Dermoscopy of a skin lesion.
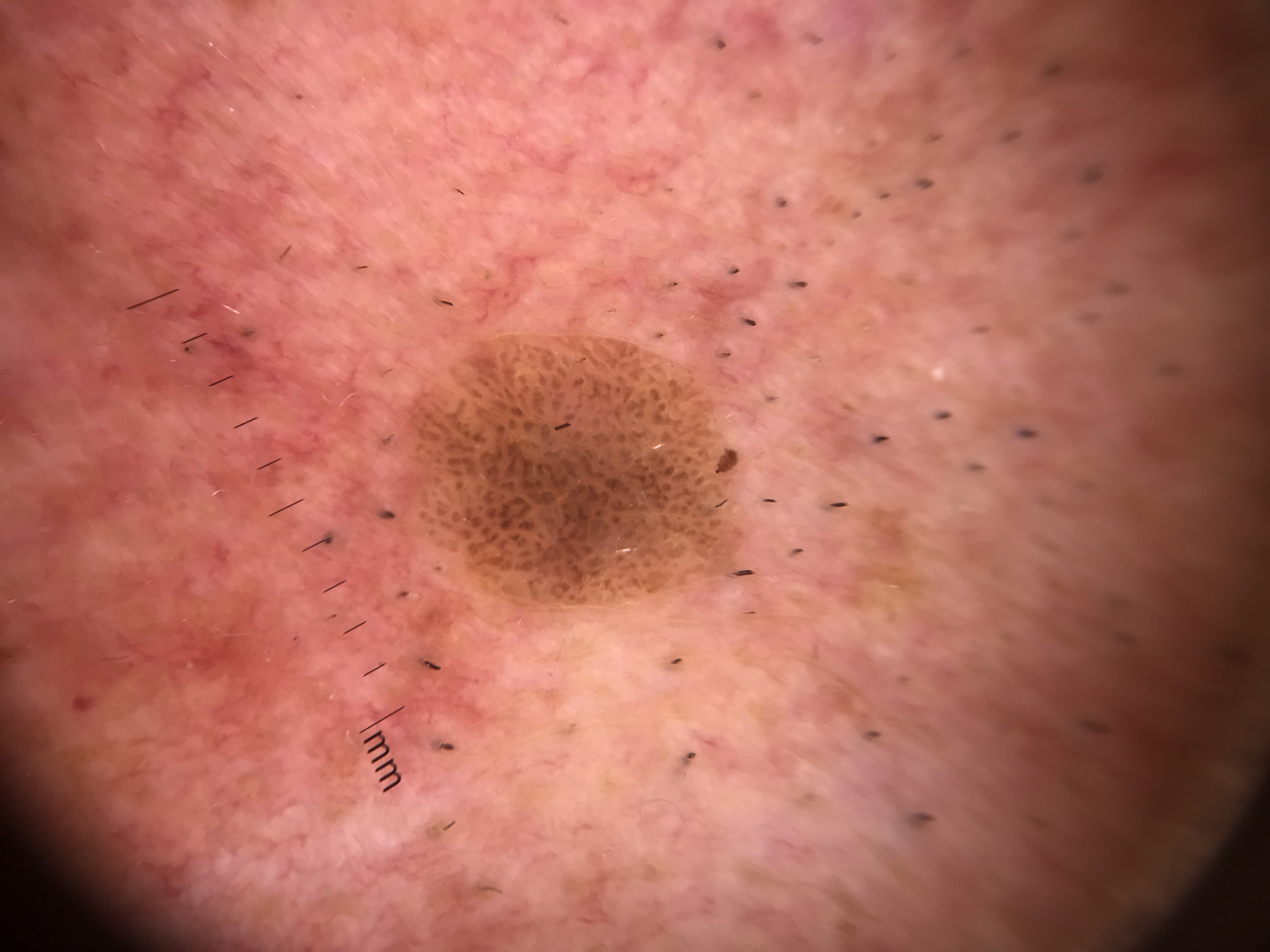Findings:
* diagnostic label: seborrheic keratosis (expert consensus)